A patient age 77 — 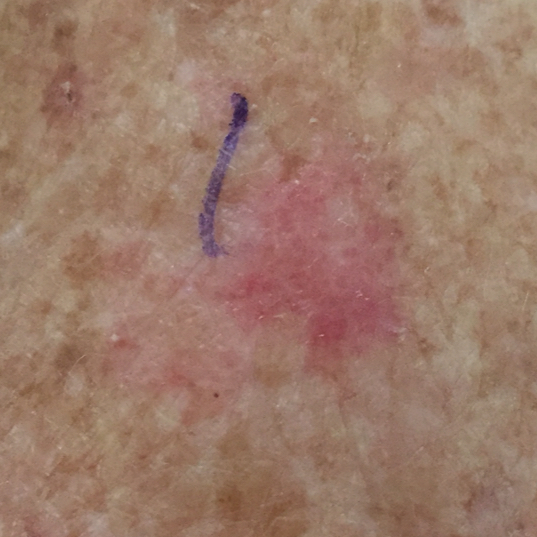  lesion_location: a forearm
  symptoms:
    present:
      - itching
      - bleeding
      - pain
  diagnosis:
    name: actinic keratosis
    code: ACK
    malignancy: indeterminate
    confirmation: clinical consensus